A skin lesion imaged with a dermatoscope. A female patient about 50 years old.
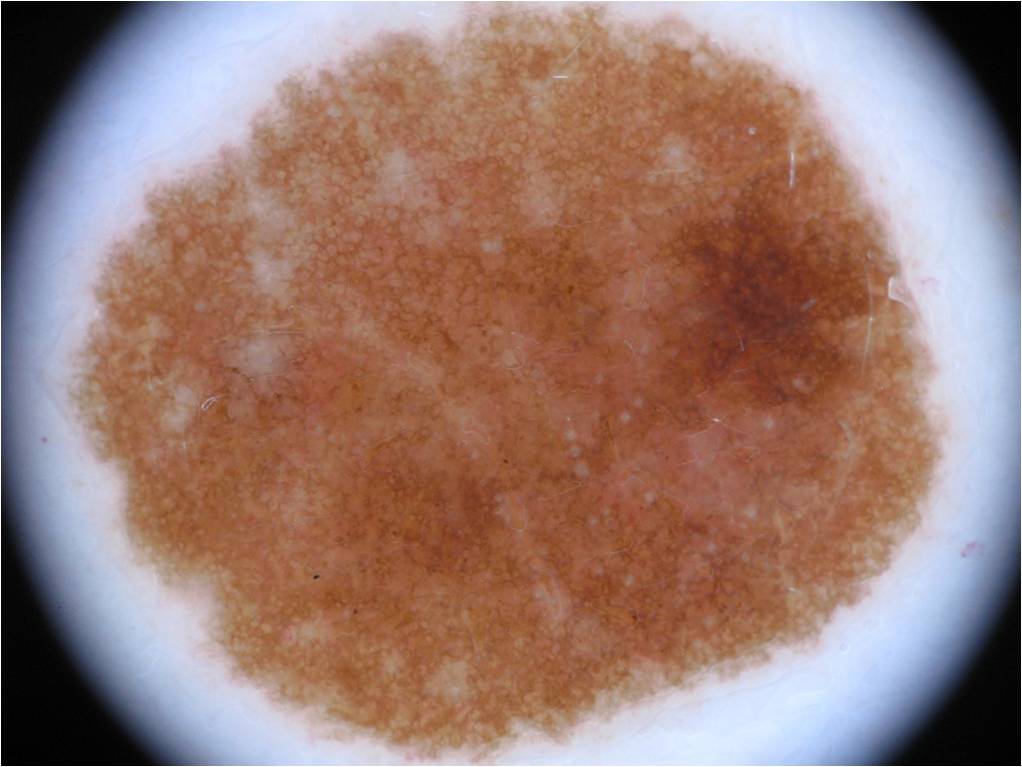– dermoscopic pattern · globules and pigment network
– bounding box · left=77, top=2, right=939, bottom=759
– diagnostic label · a melanocytic nevus